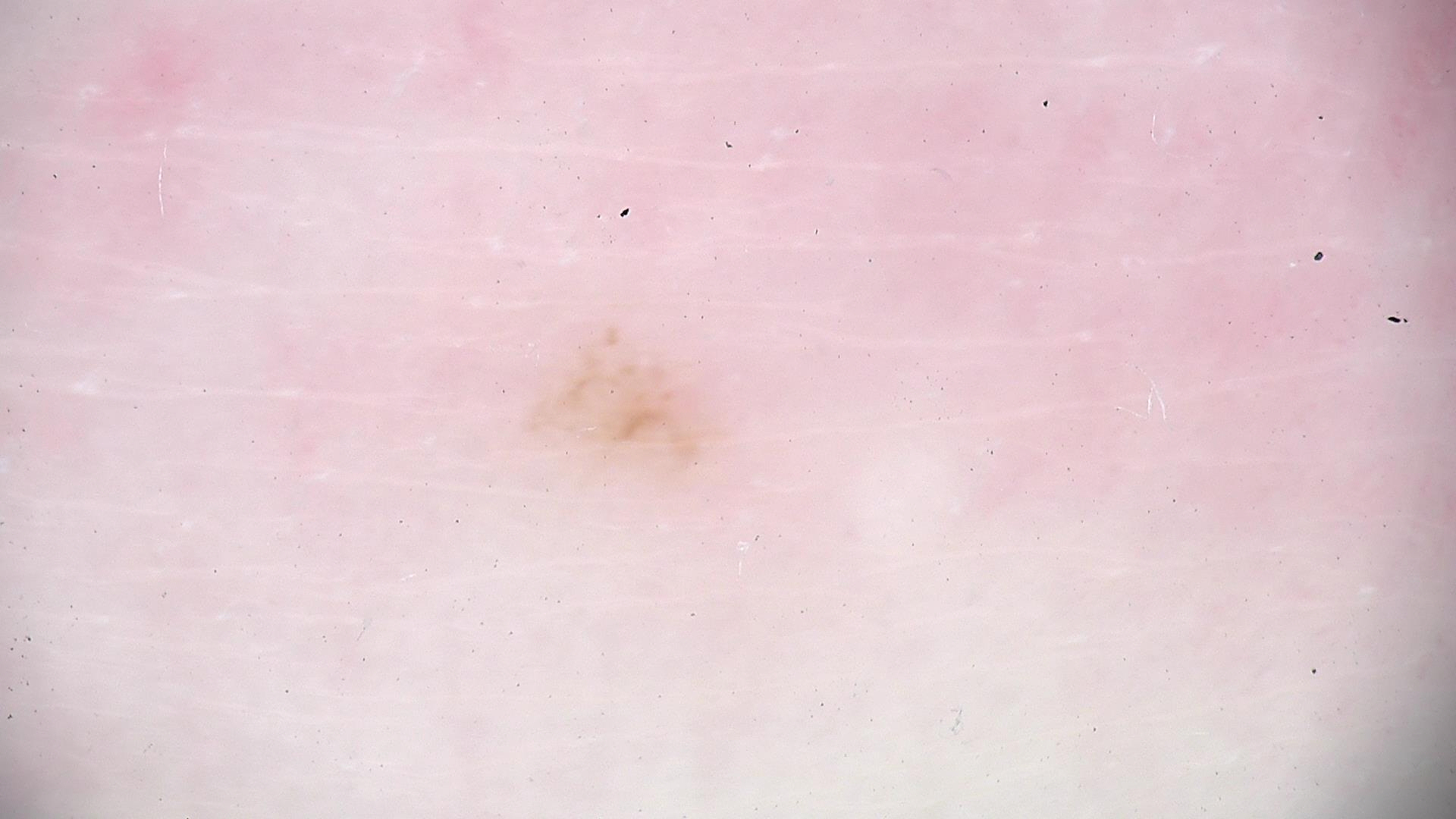| field | value |
|---|---|
| imaging | dermatoscopy |
| label | acral dysplastic junctional nevus (expert consensus) |